The photograph was taken at an angle. Skin tone: Fitzpatrick IV; human graders estimated Monk Skin Tone 6 (US pool) or 4 (India pool). Female patient, age 18–29.
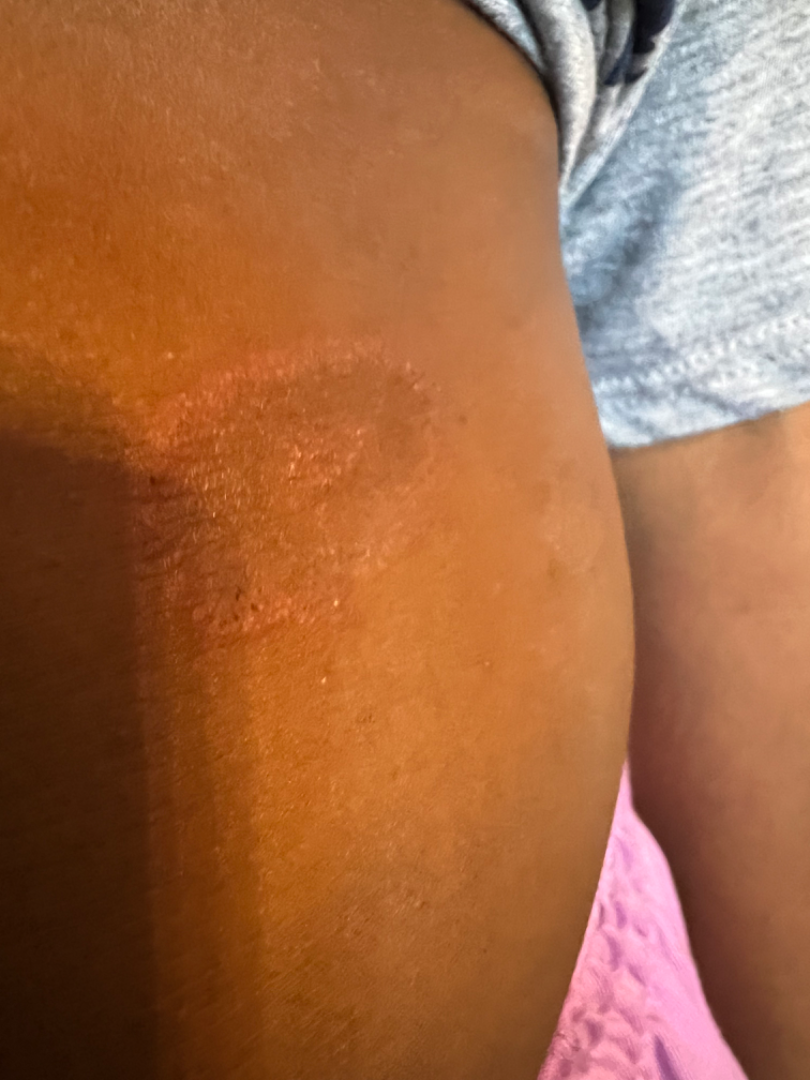Findings: Tinea (weight 0.55); Drug Rash (weight 0.27); Porokeratosis (weight 0.18).